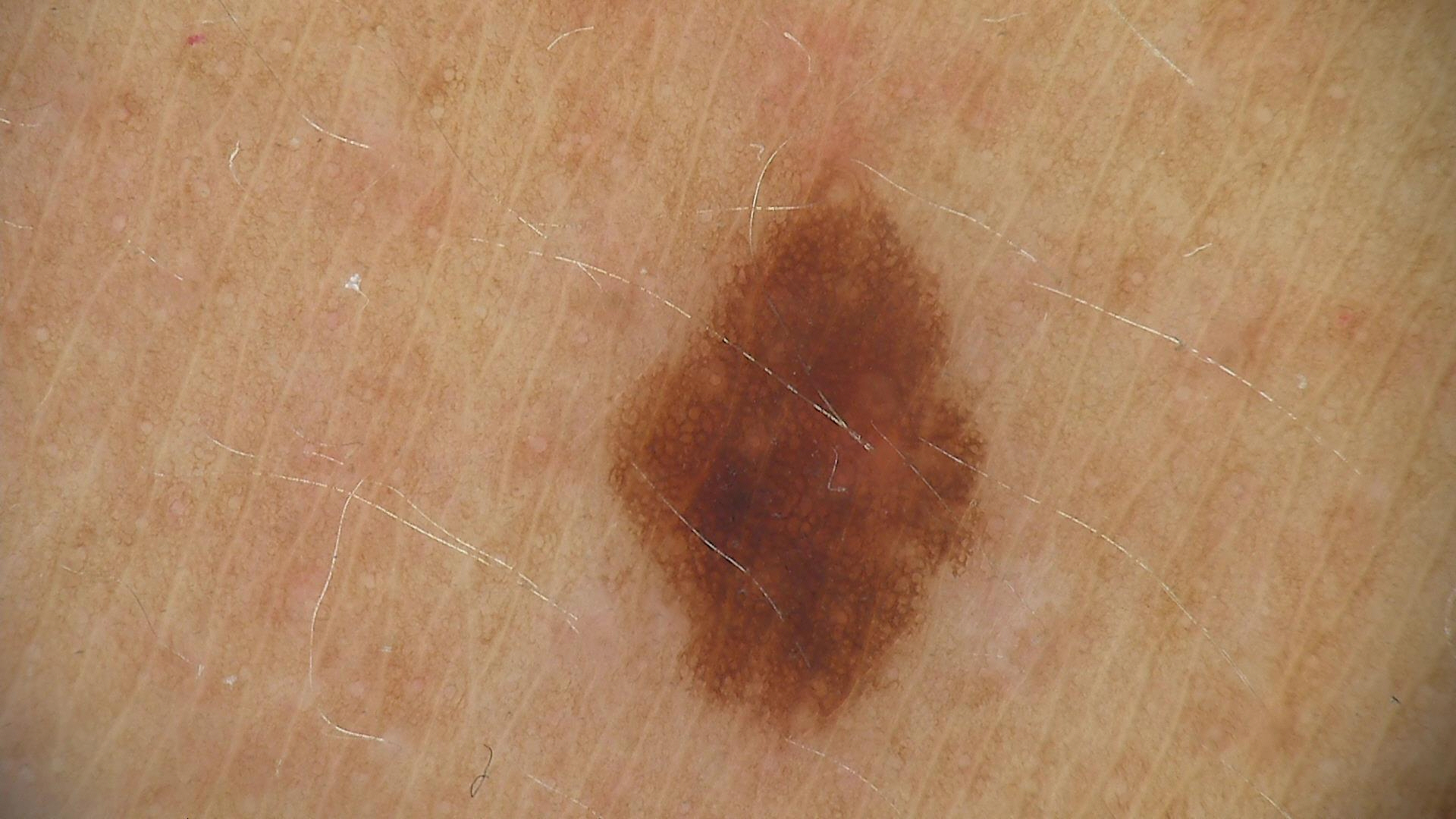Labeled as a benign lesion — a dysplastic junctional nevus.